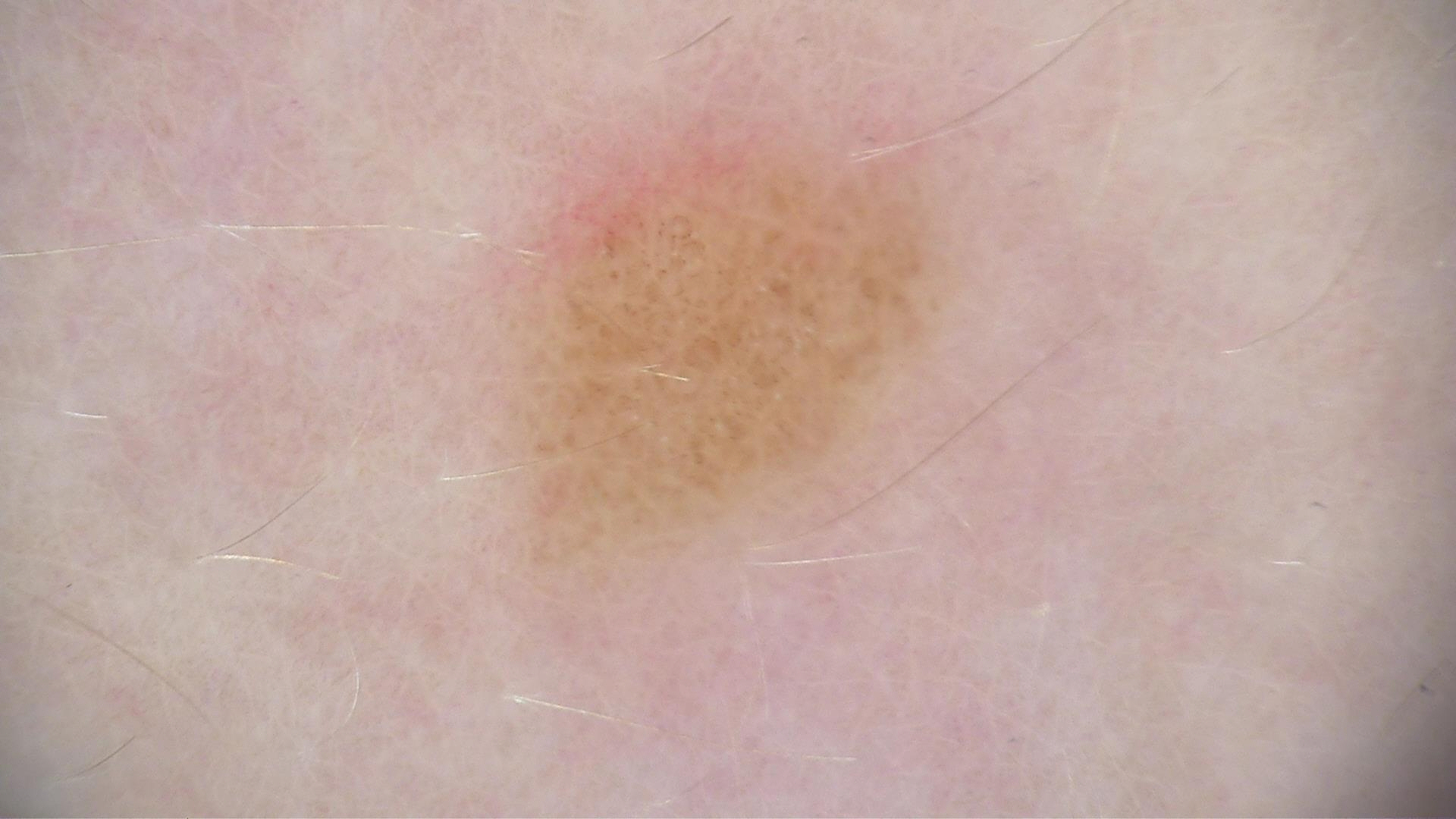imaging: dermatoscopy; category: banal; class: compound nevus (expert consensus).